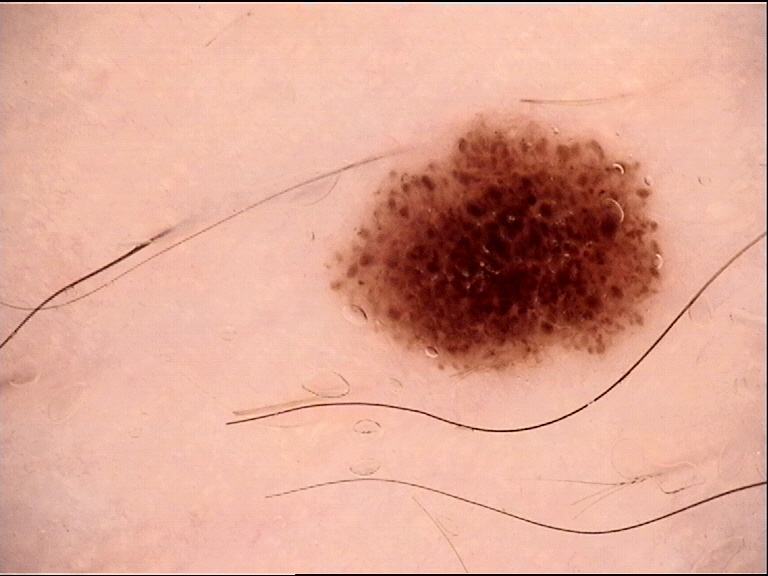Findings: A dermoscopy image of a single skin lesion. This is a banal lesion. Impression: The diagnosis was a compound nevus.